The photograph was taken at an angle.
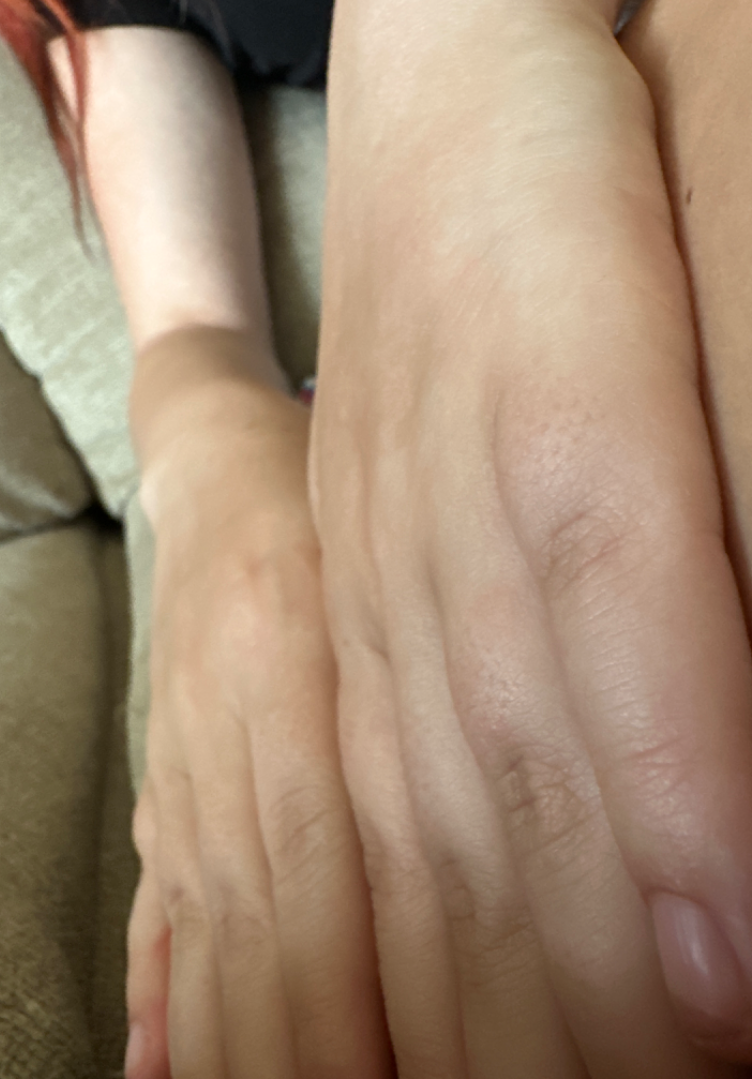Review:
The dermatologist found no clearly identifiable skin pathology in the image.